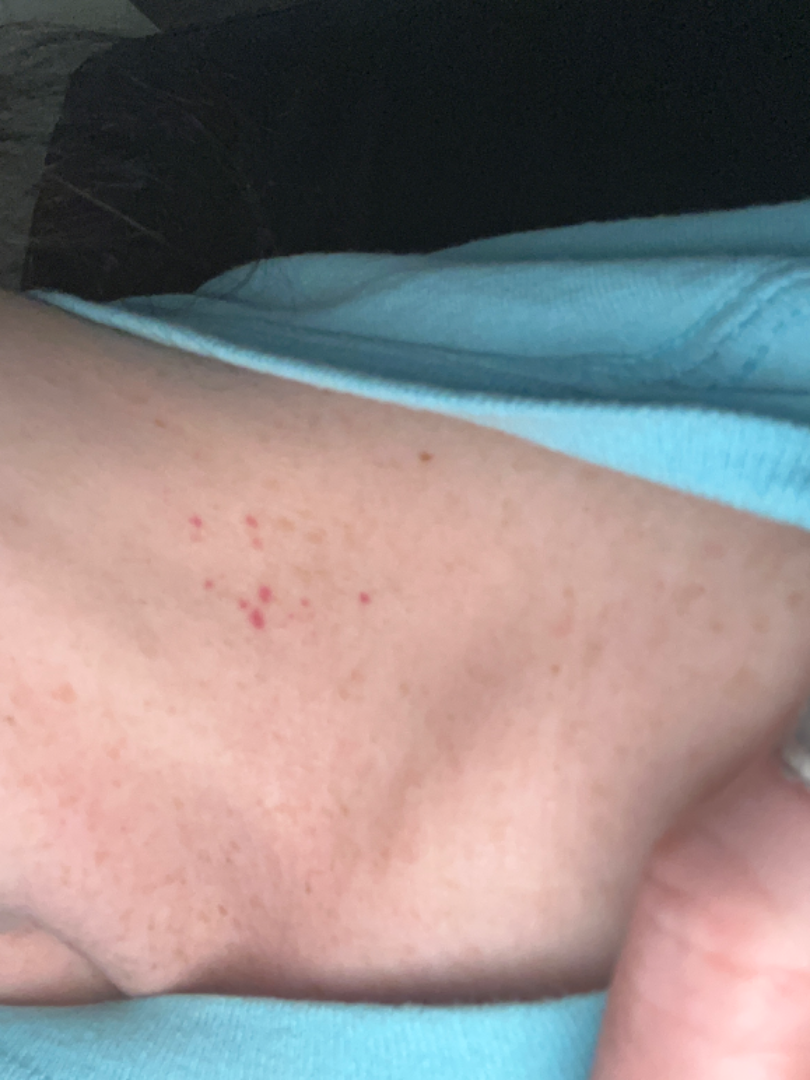The skin condition could not be confidently assessed from this image. The photograph was taken at an angle. The head or neck is involved.